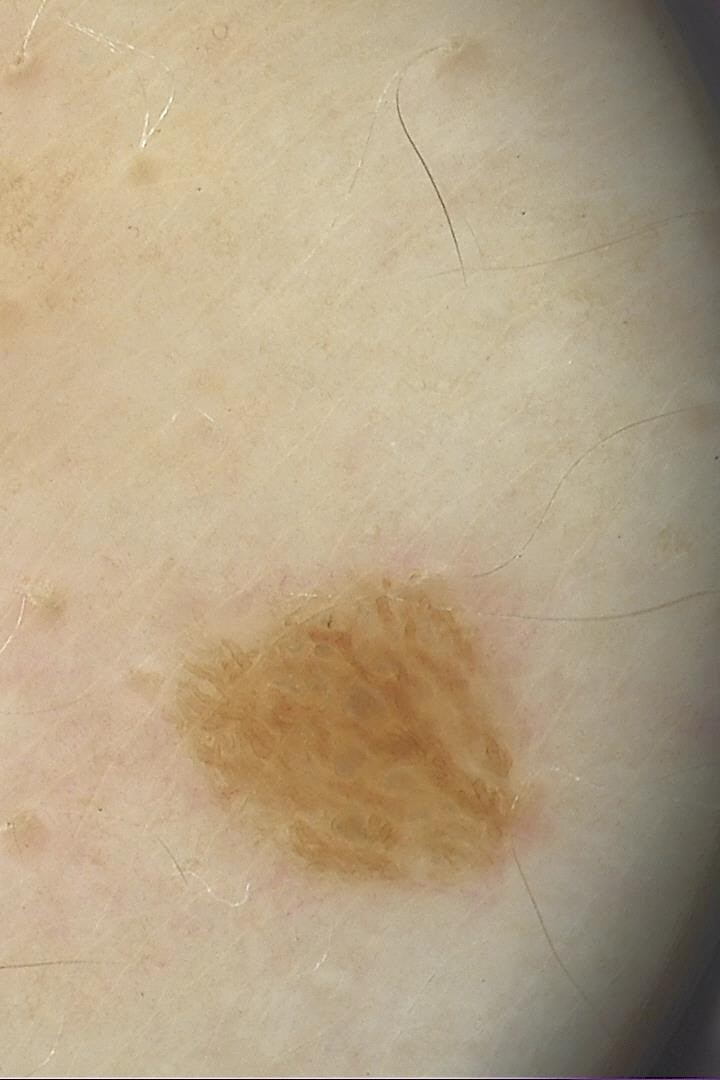Conclusion: Labeled as a seborrheic keratosis.